A female subject in their early 70s · a clinical photo of a skin lesion taken with a smartphone: 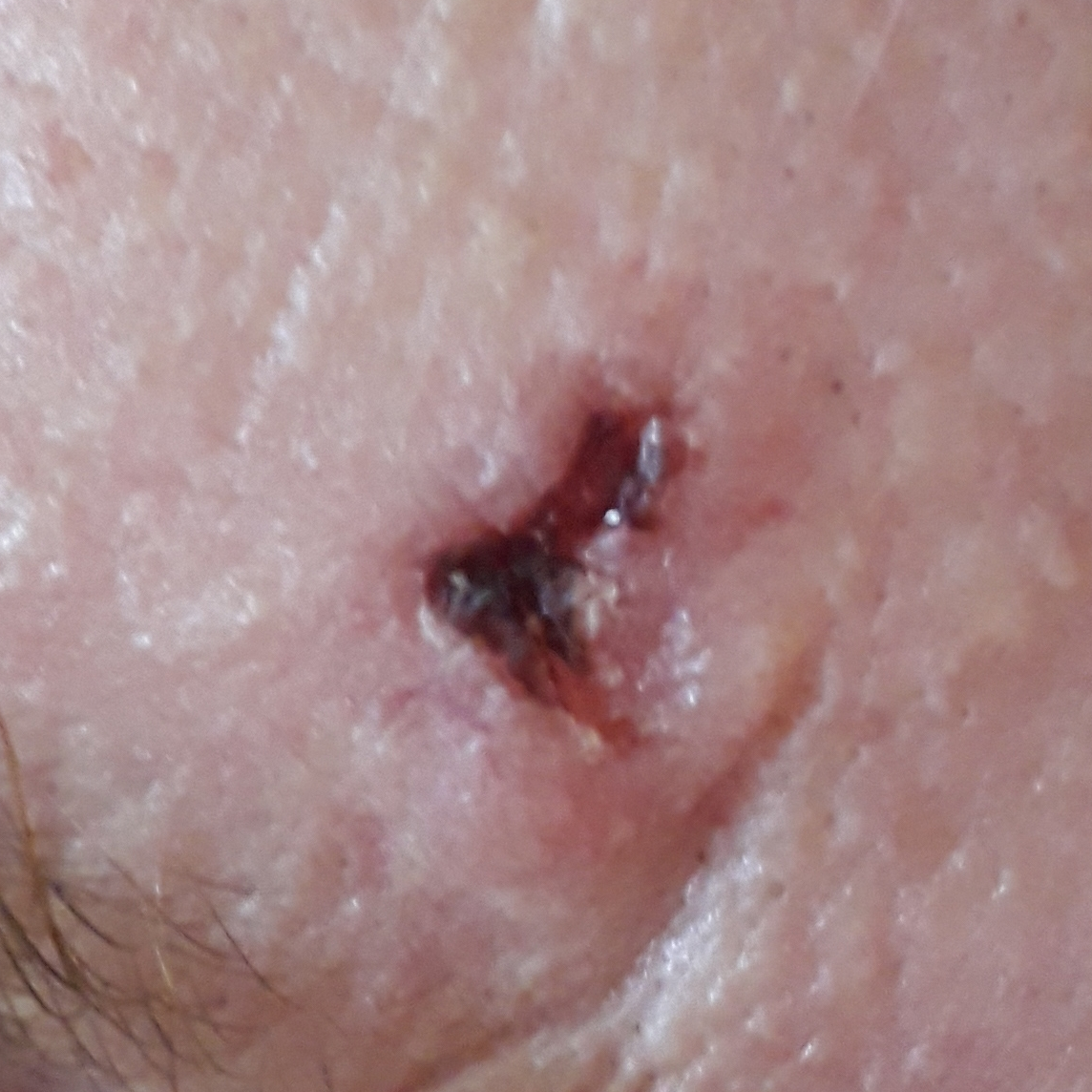Located on the face.
By the patient's account, the lesion has bled, is elevated, hurts, and itches.
On biopsy, the diagnosis was a basal cell carcinoma.